A female subject in their mid- to late 60s · contact-polarized dermoscopy of a skin lesion: 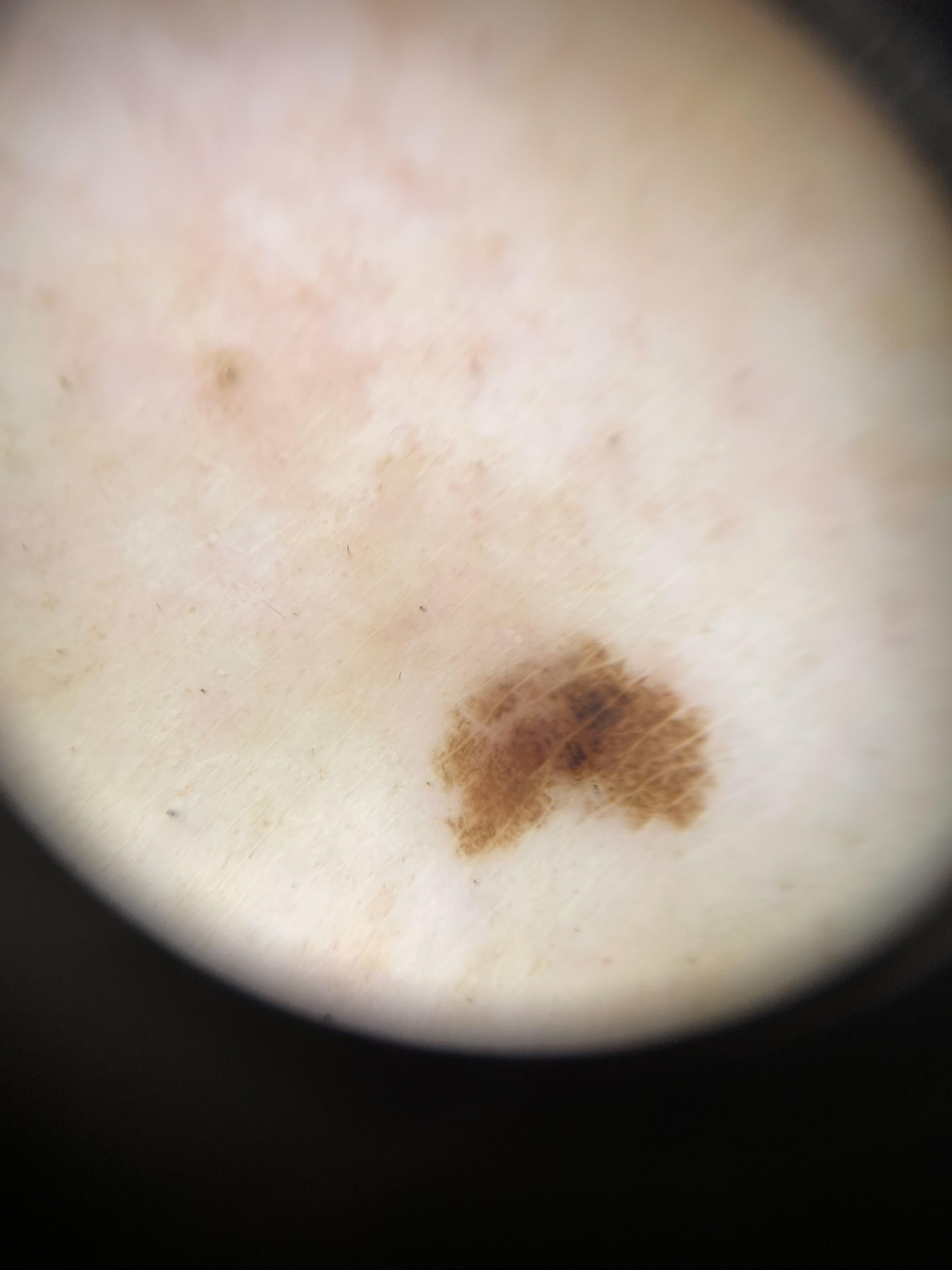anatomic site: a lower extremity, pathology: Melanoma (biopsy-proven).